Referred with a clinical suspicion of basal cell carcinoma · a macroscopic clinical photograph of a skin lesion · a female subject age 48.
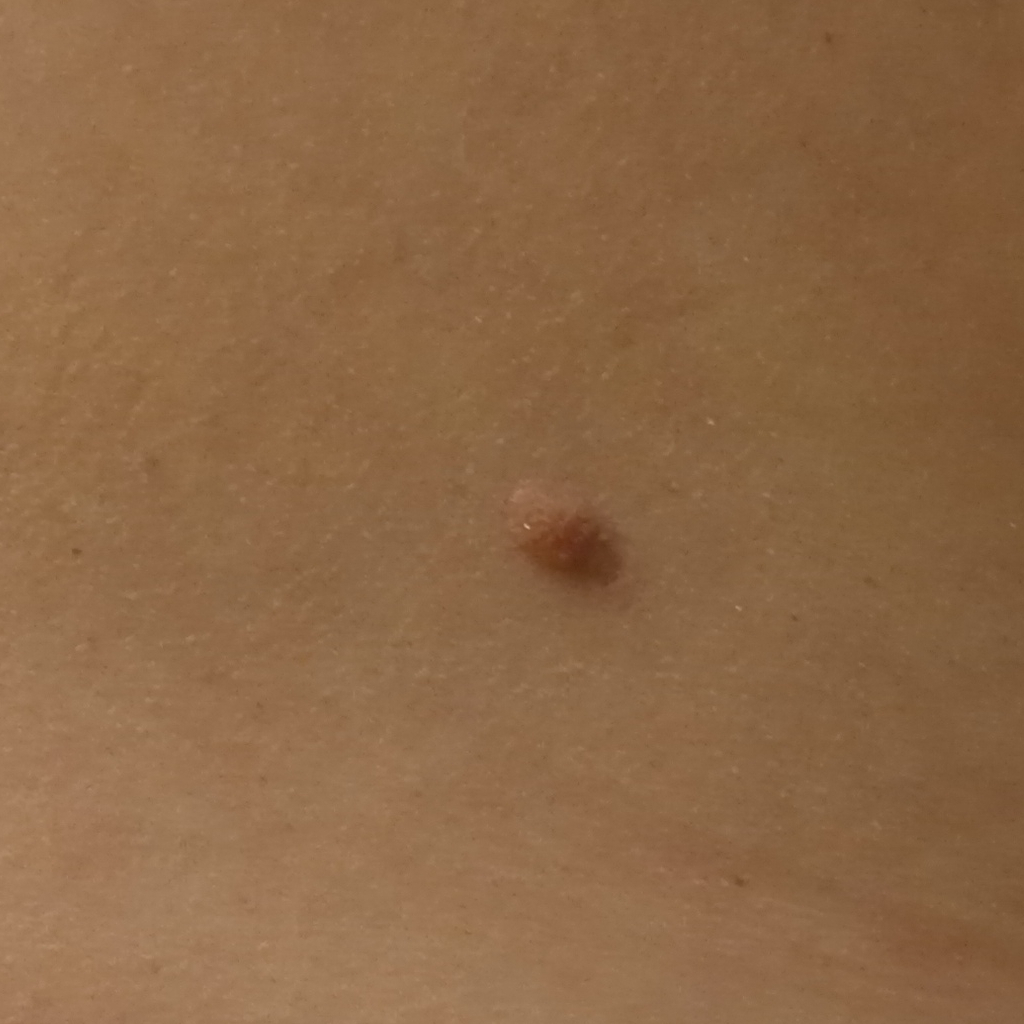The lesion involves the back.
The lesion is about 12.3 mm across.
Histopathologically confirmed as a basal cell carcinoma, following excision, with tumor thickness 1.1 mm.